A patient in their early 80s · a clinical photo of a skin lesion taken with a smartphone — 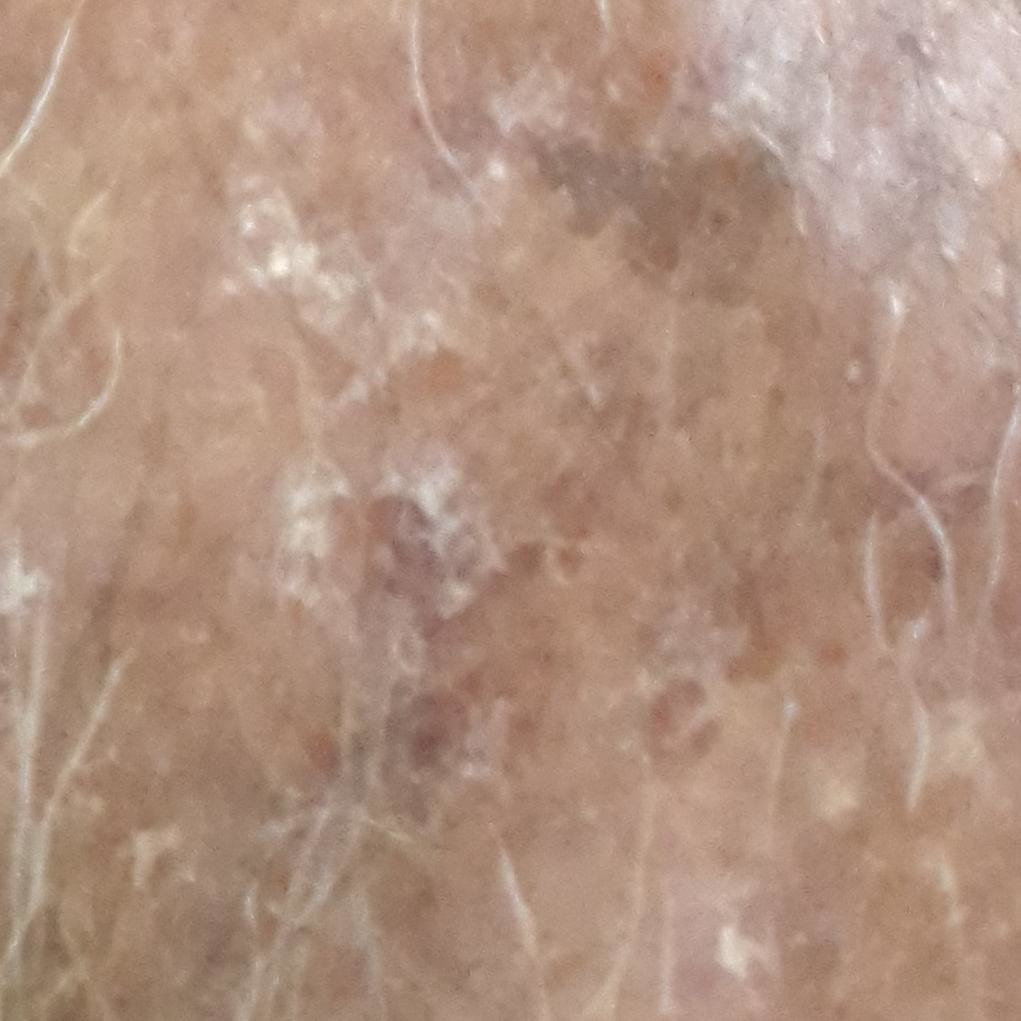body site = a forearm; patient-reported symptoms = itching; impression = actinic keratosis (clinical consensus).